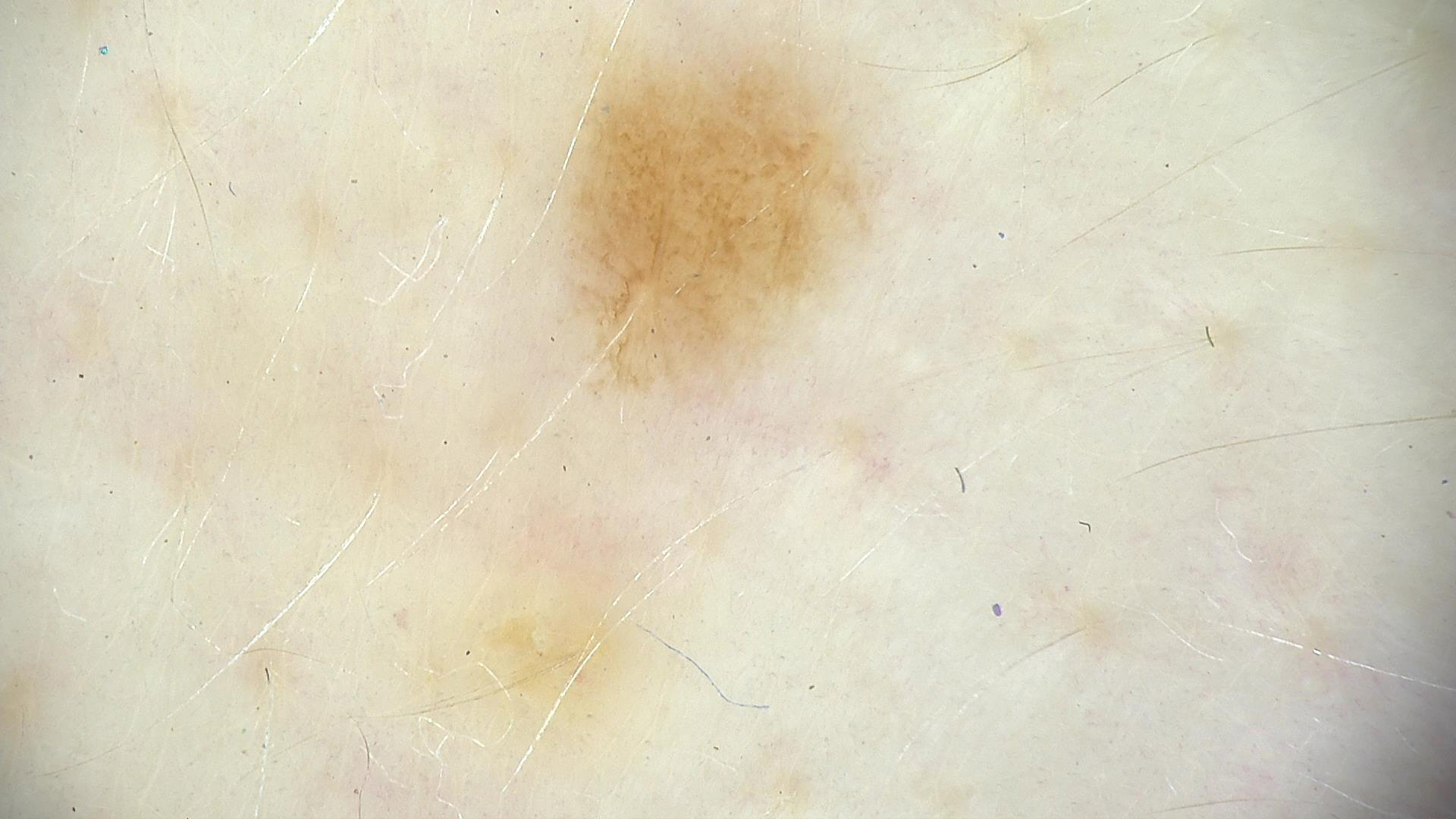Dermoscopy of a skin lesion. Labeled as a dysplastic junctional nevus.